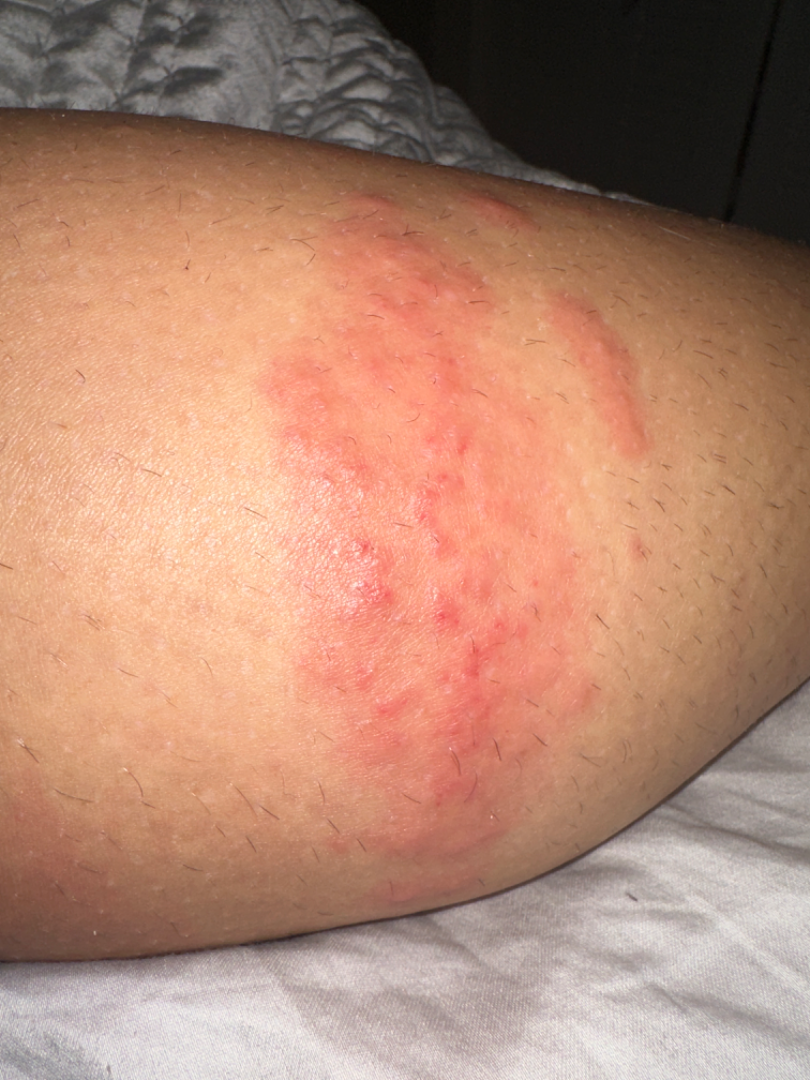The image was not sufficient for the reviewer to characterize the skin condition. A close-up photograph. The contributor notes the condition has been present for one to four weeks. Reported lesion symptoms include enlargement, itching and bothersome appearance. The lesion involves the leg. The patient described the issue as a rash. Skin tone: Fitzpatrick skin type IV; non-clinician graders estimated MST 2 or 3 (two reviewer pools).